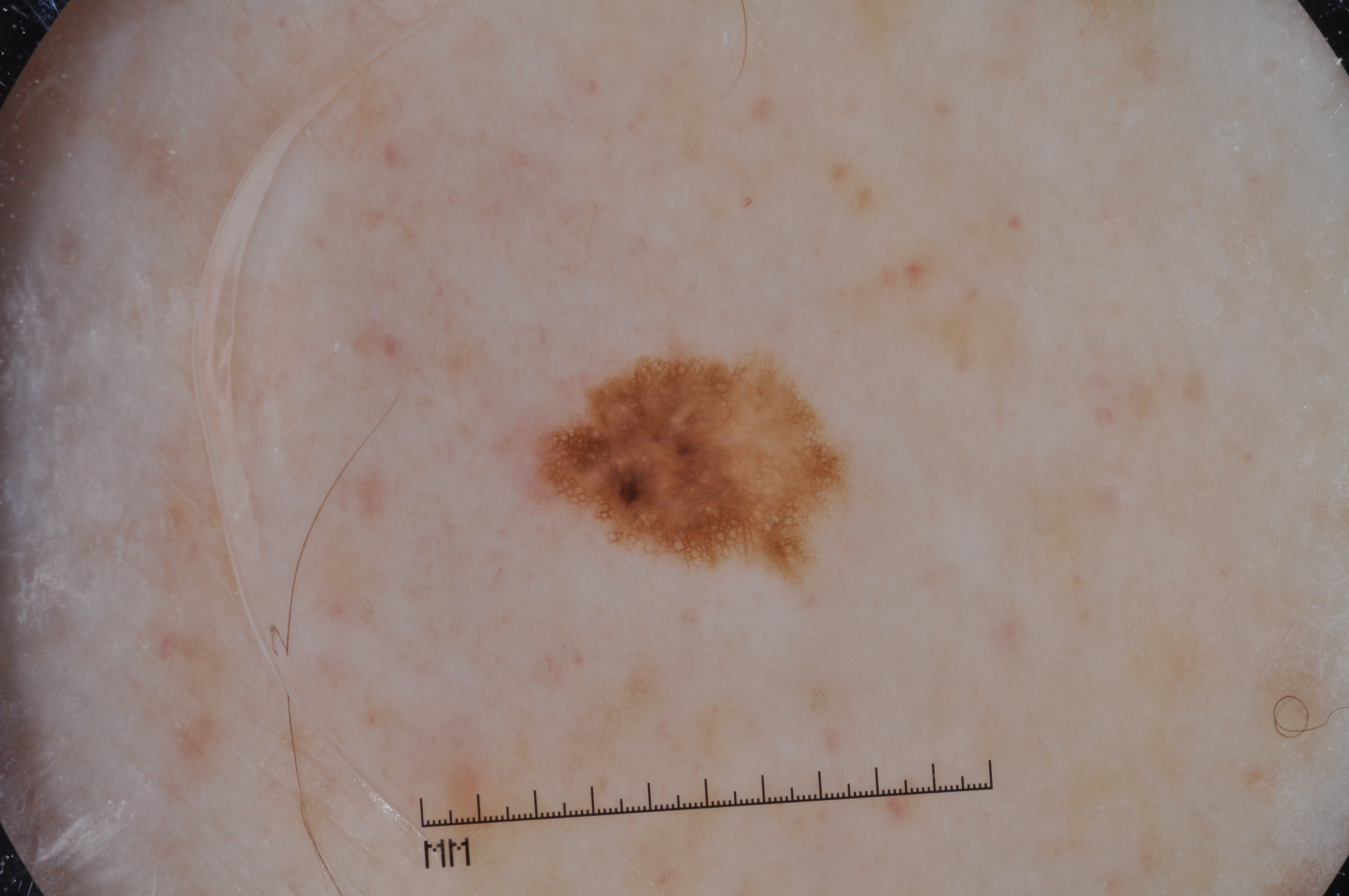Dermoscopy of a skin lesion.
The lesion takes up about 4% of the image.
Dermoscopic review identifies pigment network.
Lesion location: x1=493, y1=338, x2=852, y2=587.
The clinical diagnosis was a melanocytic nevus.